A close-up photograph. Skin tone: Fitzpatrick V — 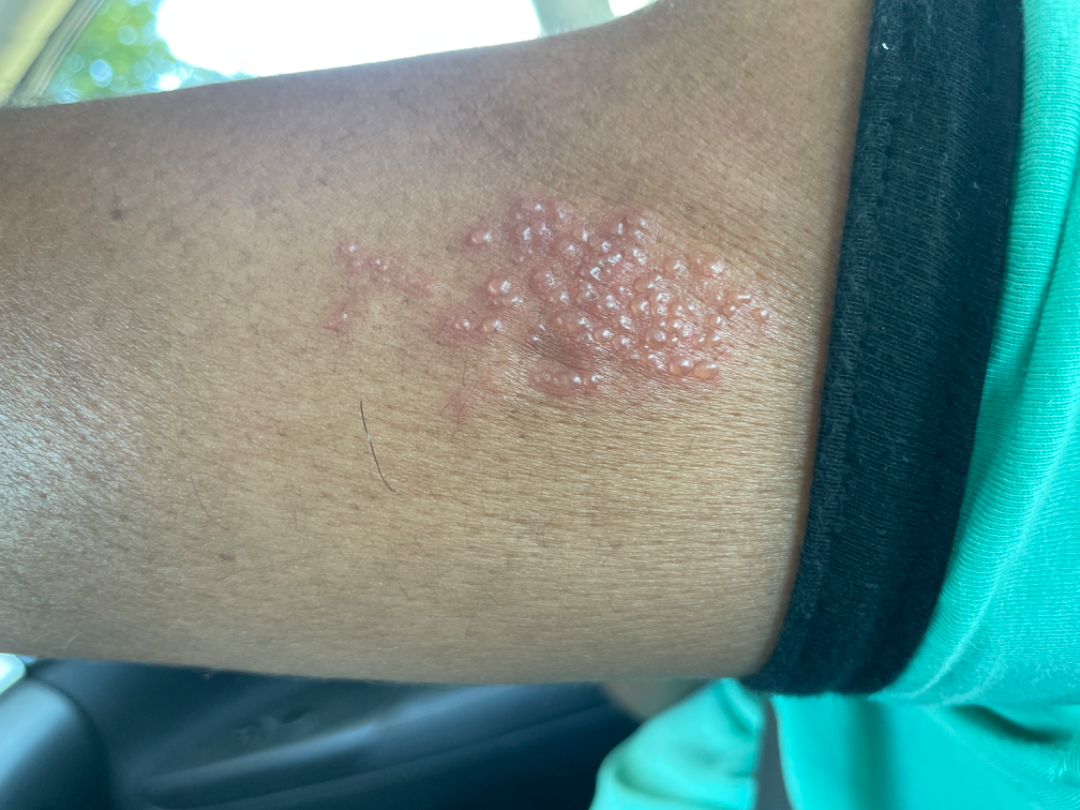On teledermatology review: the leading consideration is Herpes Simplex; the differential also includes Herpes Zoster.